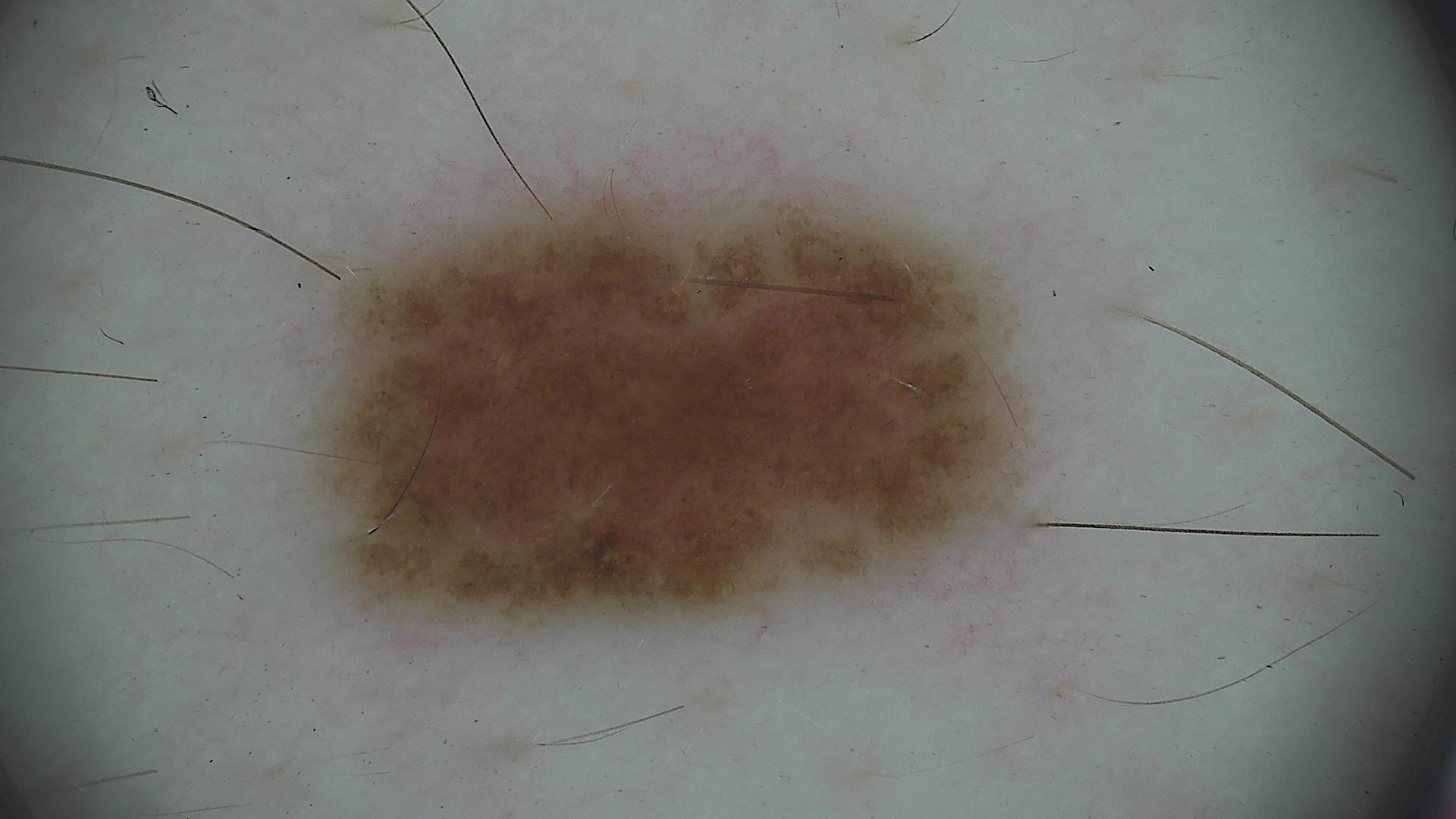{"diagnosis": {"name": "dysplastic junctional nevus", "code": "jd", "malignancy": "benign", "super_class": "melanocytic", "confirmation": "expert consensus"}}